The patient is skin type II.
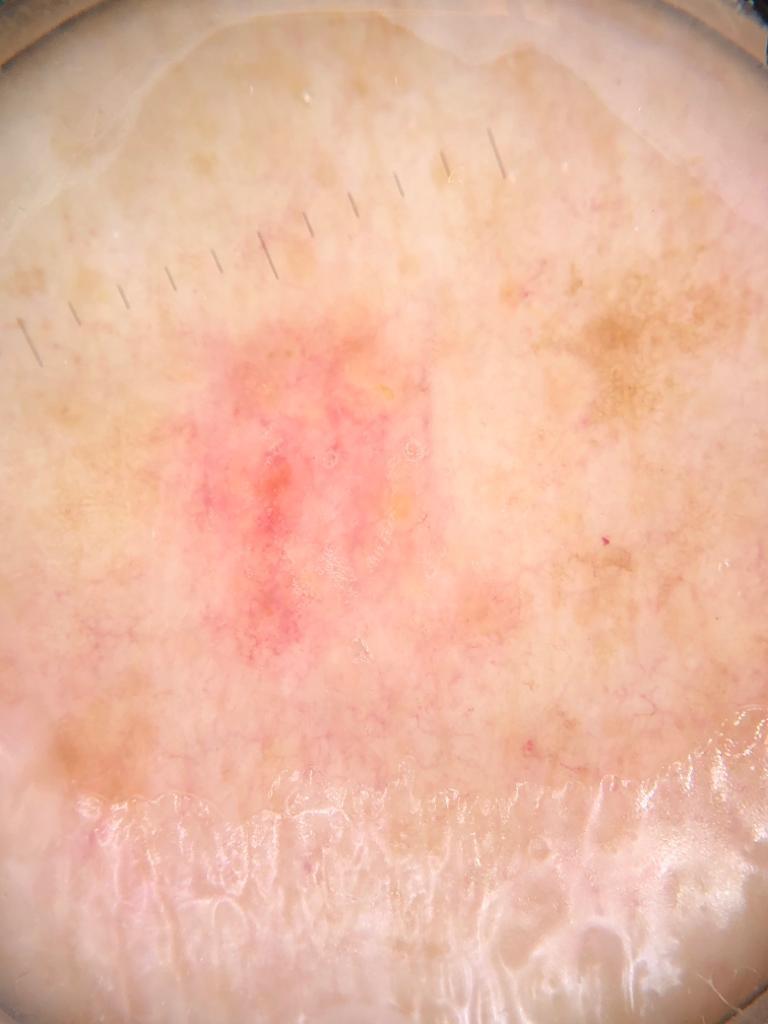The lesion is located on the trunk. Confirmed on histopathology as a malignant, adnexal lesion — a basal cell carcinoma.